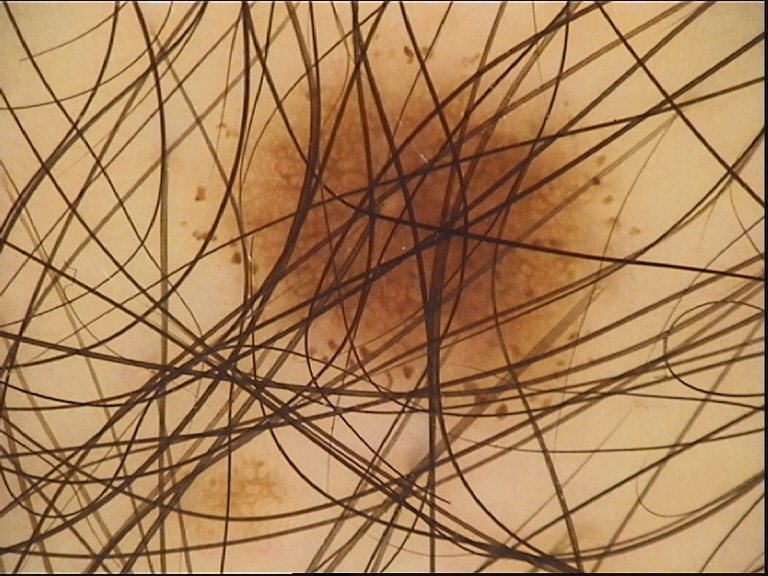A dermatoscopic image of a skin lesion. Labeled as a benign lesion — a dysplastic junctional nevus.